The lesion involves the head or neck, back of the hand, palm and arm · this is a close-up image · female contributor, age 18–29.
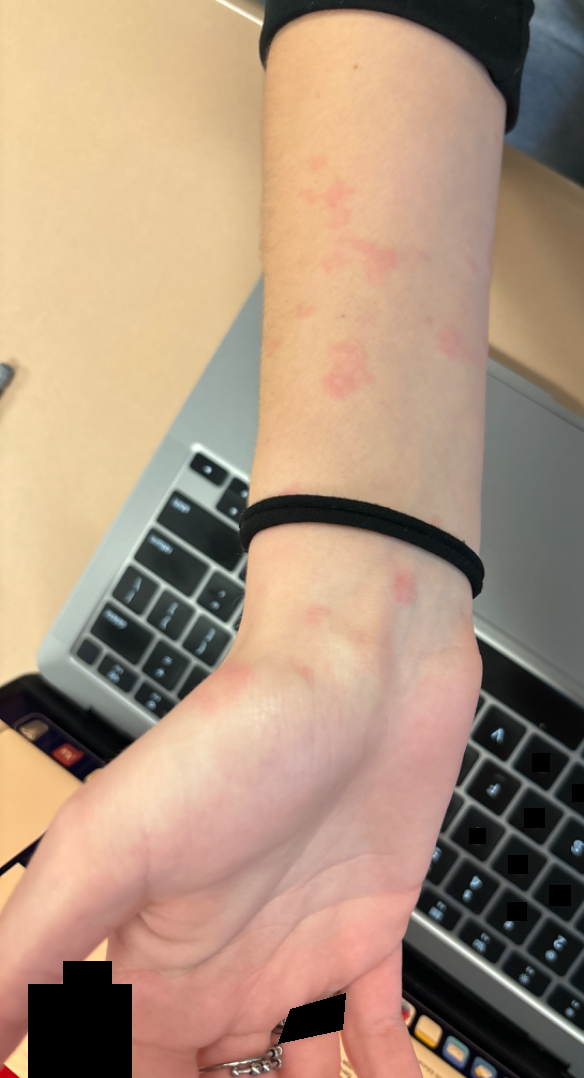differential: Urticaria (67%); Hypersensitivity (33%).